A dermoscopy image of a single skin lesion:
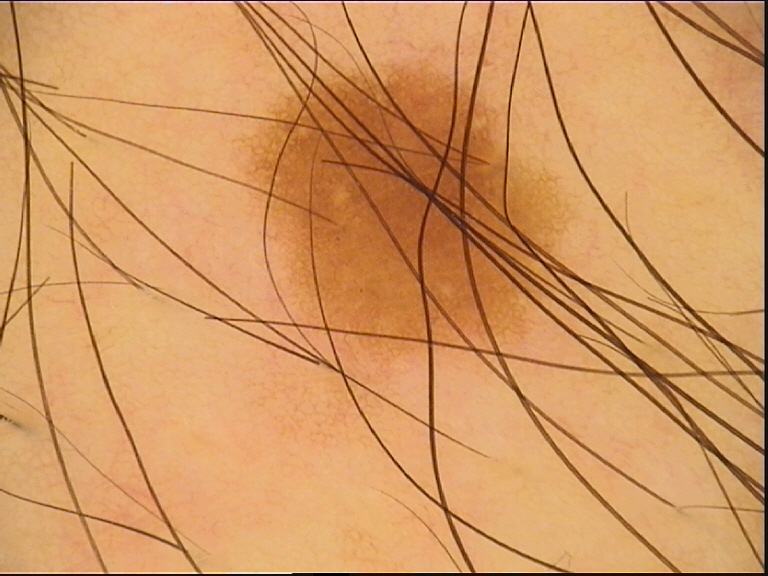Classified as a banal lesion — a junctional nevus.